Dermoscopy of a skin lesion.
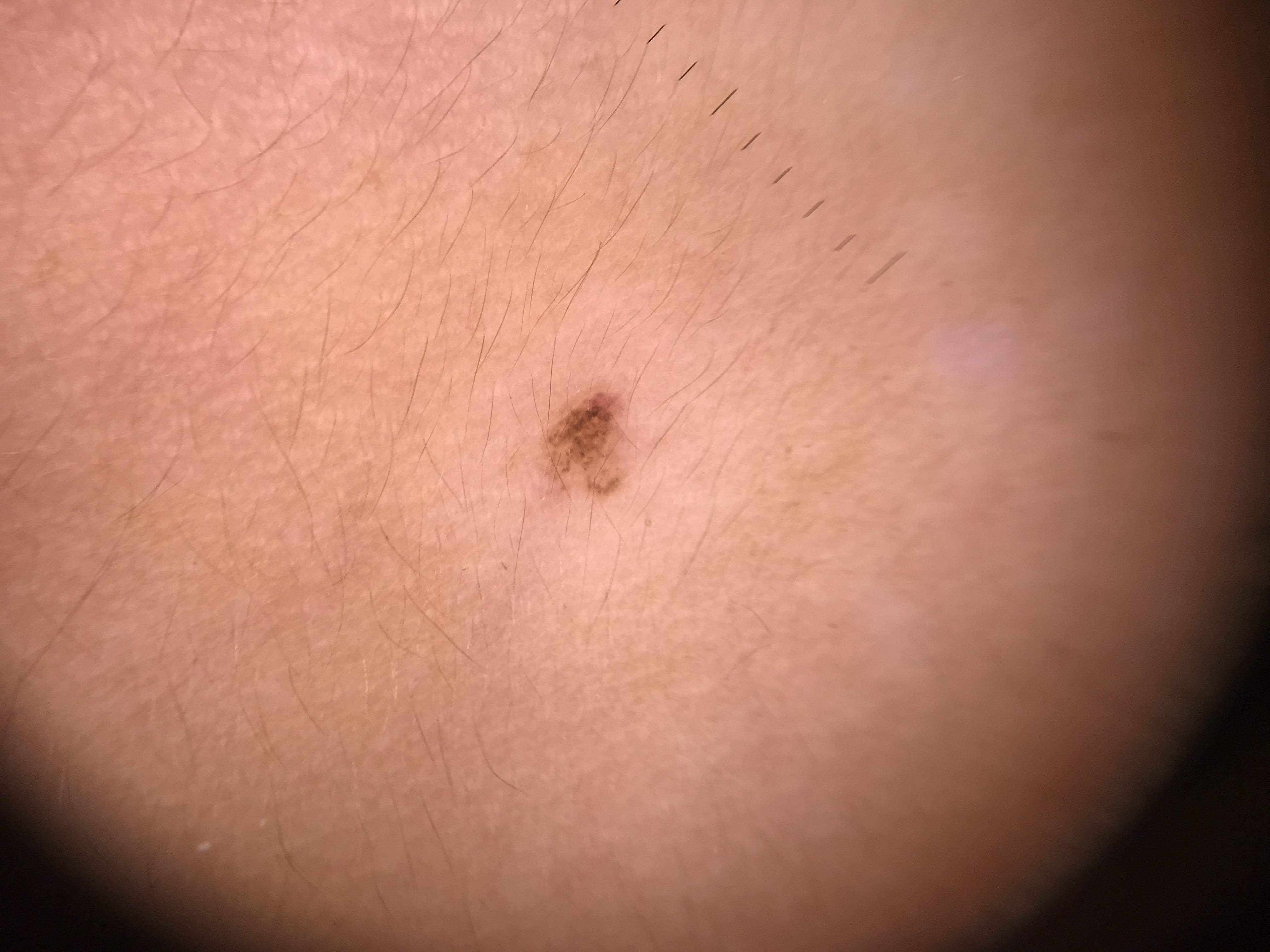assessment: dysplastic junctional nevus (expert consensus).